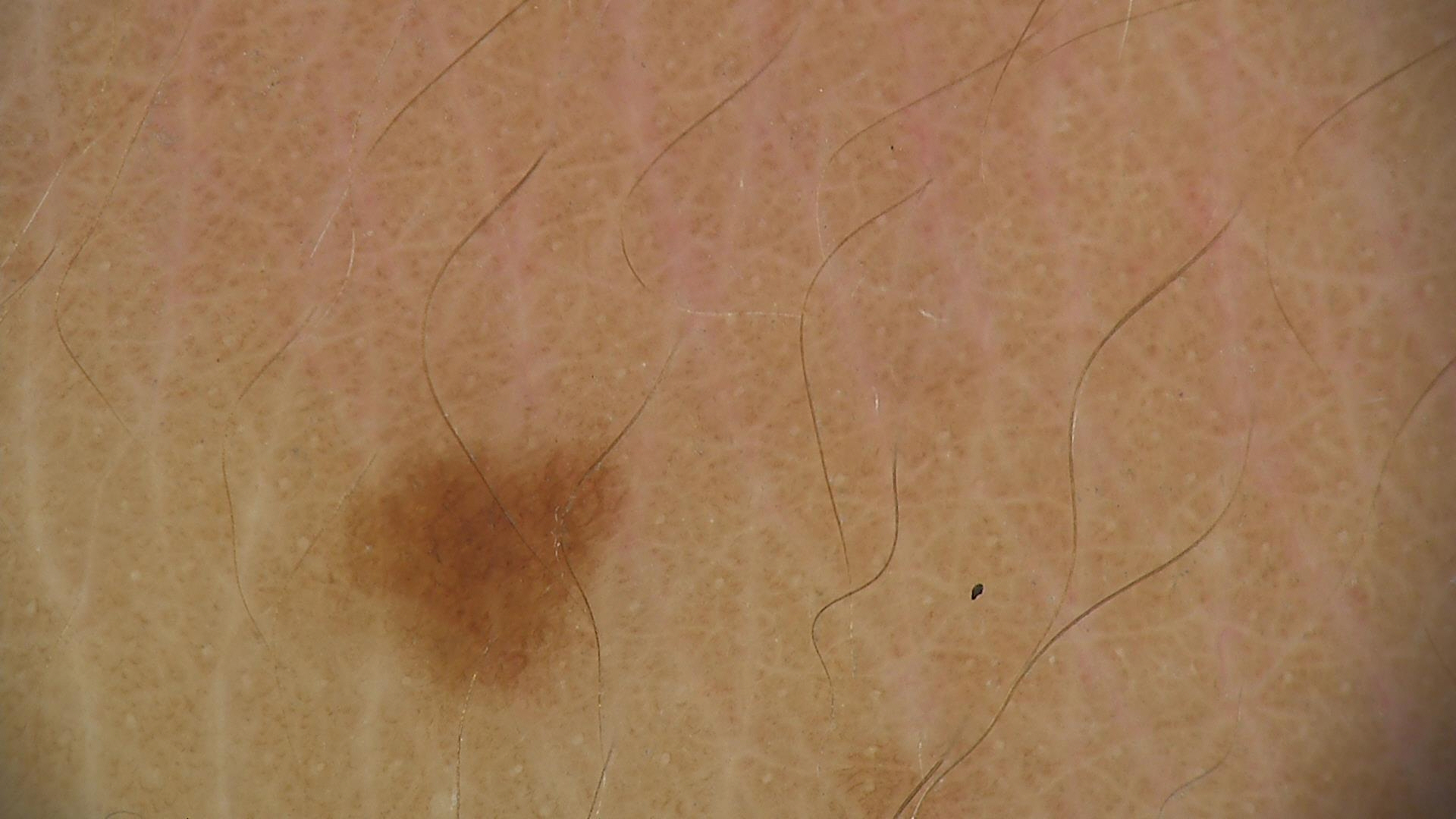lesion type = banal | label = junctional nevus (expert consensus).